A patient in their 40s · a clinical close-up photograph of a skin lesion:
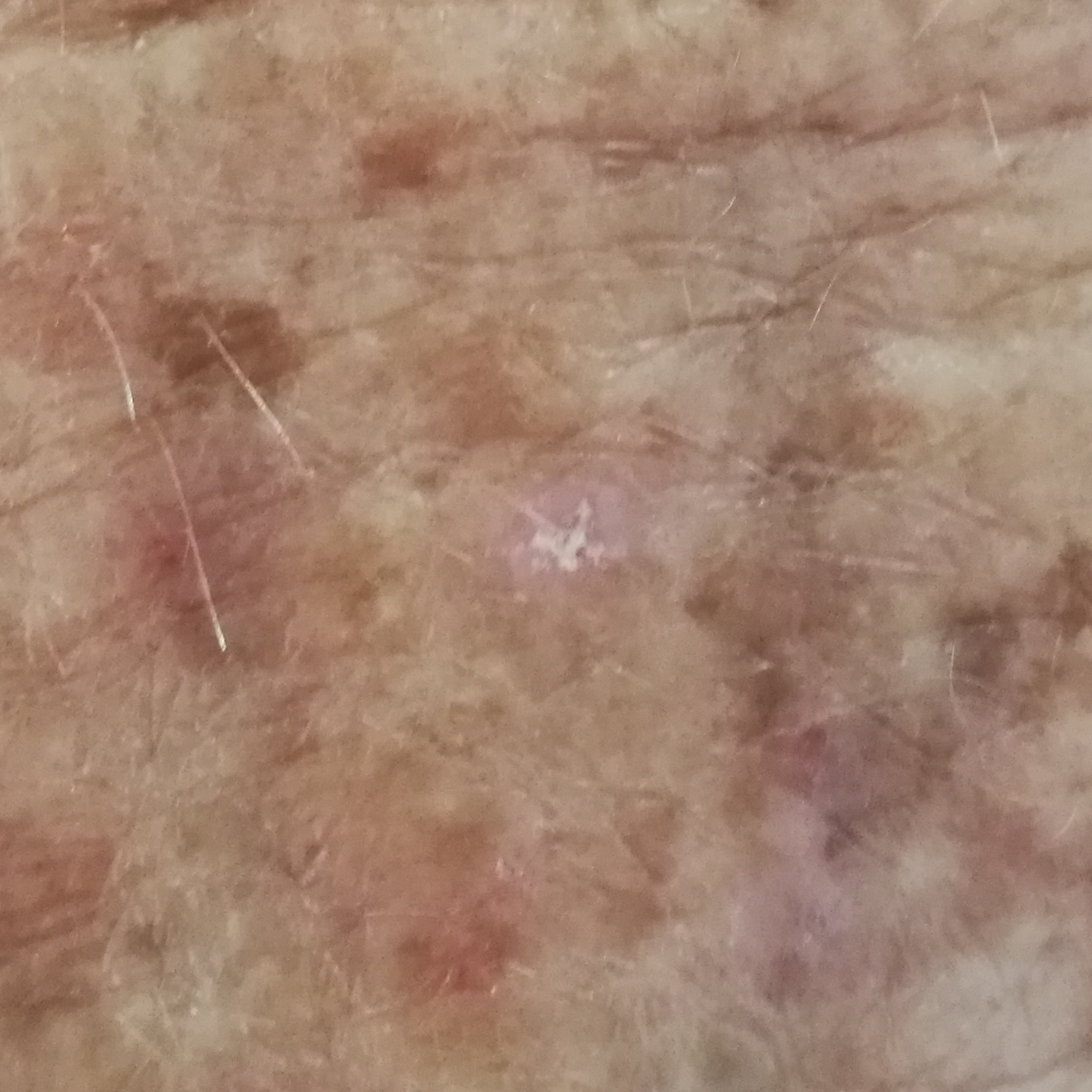<lesion>
  <symptoms>
    <present>itching, growth</present>
  </symptoms>
  <diagnosis>
    <name>actinic keratosis</name>
    <code>ACK</code>
    <malignancy>indeterminate</malignancy>
    <confirmation>clinical consensus</confirmation>
  </diagnosis>
</lesion>